A dermoscopy image of a single skin lesion: 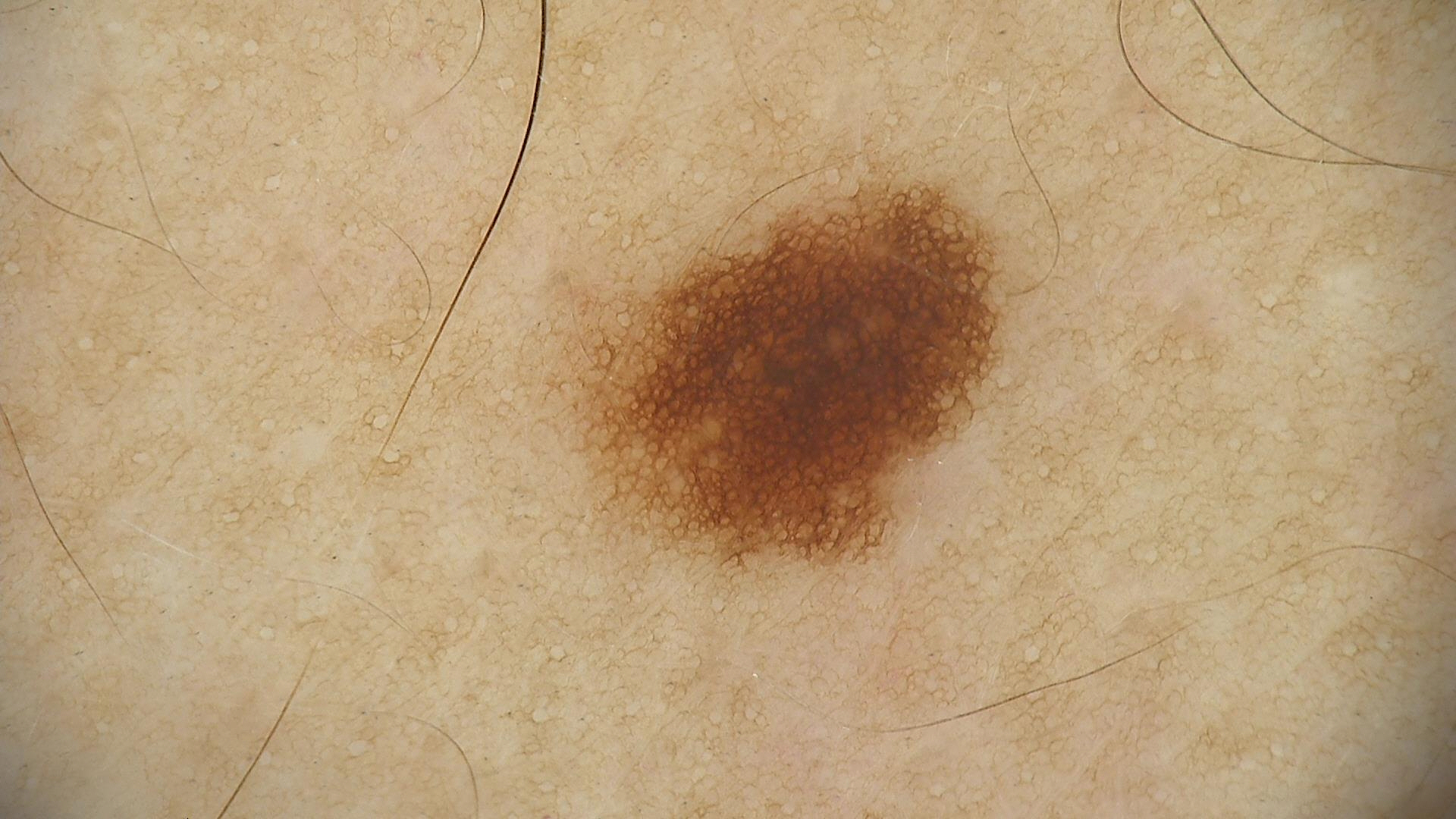Conclusion:
Labeled as a benign lesion — a dysplastic junctional nevus.